A close-up photograph:
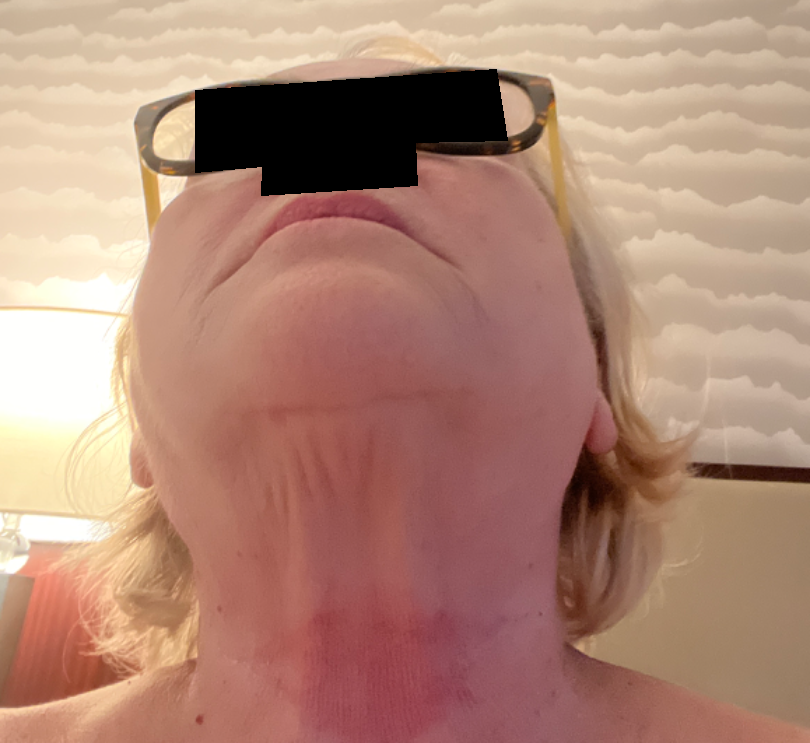Case summary:
• impression: the leading consideration is Irritant Contact Dermatitis; the differential also includes Allergic Contact Dermatitis